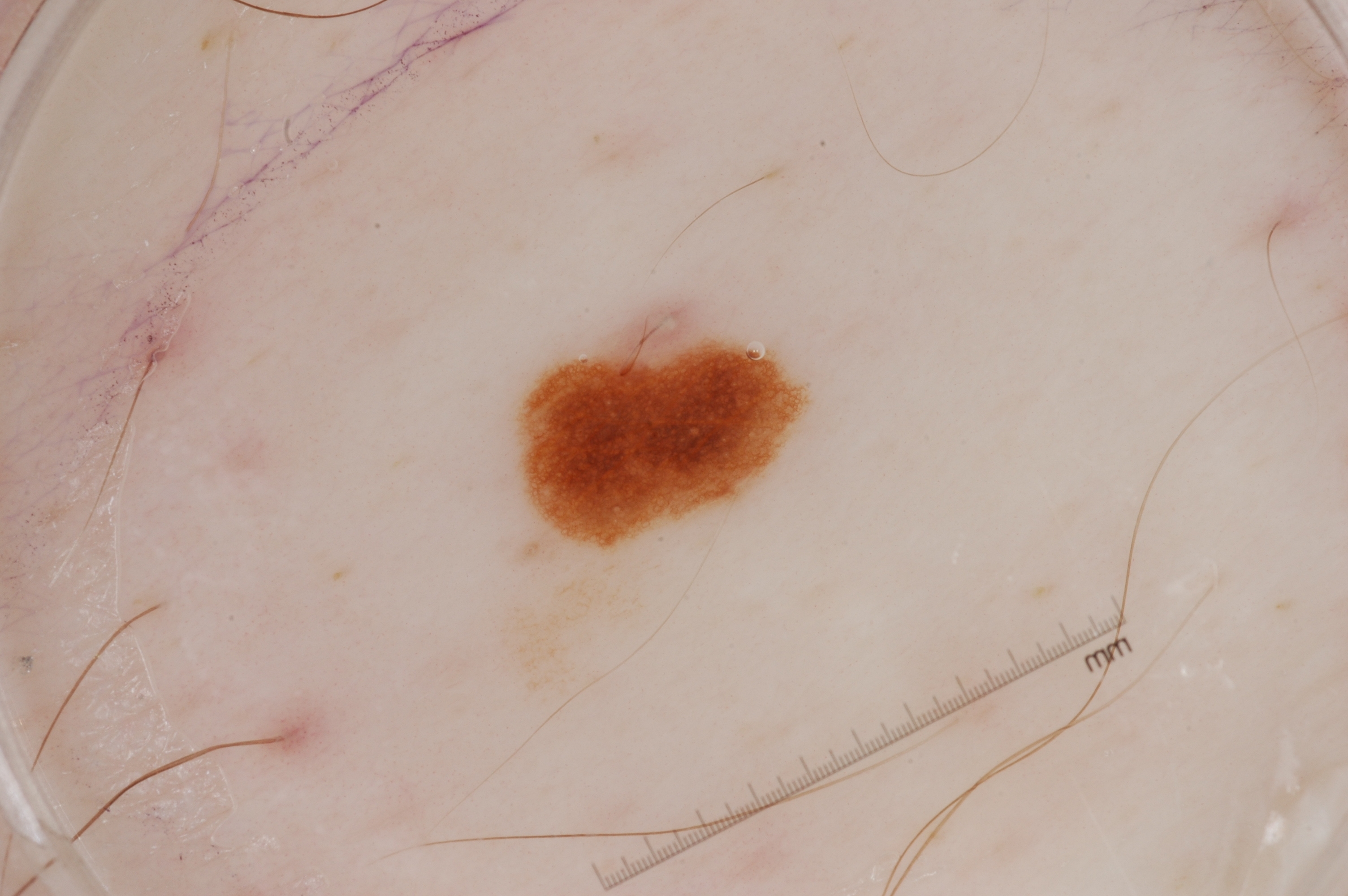Q: What is the imaging modality?
A: dermoscopic image
Q: Where is the lesion located?
A: bbox(516, 315, 801, 546)
Q: What does dermoscopy show?
A: pigment network and milia-like cysts; absent: streaks and negative network
Q: How large is the lesion within the image?
A: ~4% of the field
Q: What did the assessment conclude?
A: a melanocytic nevus, a benign skin lesion